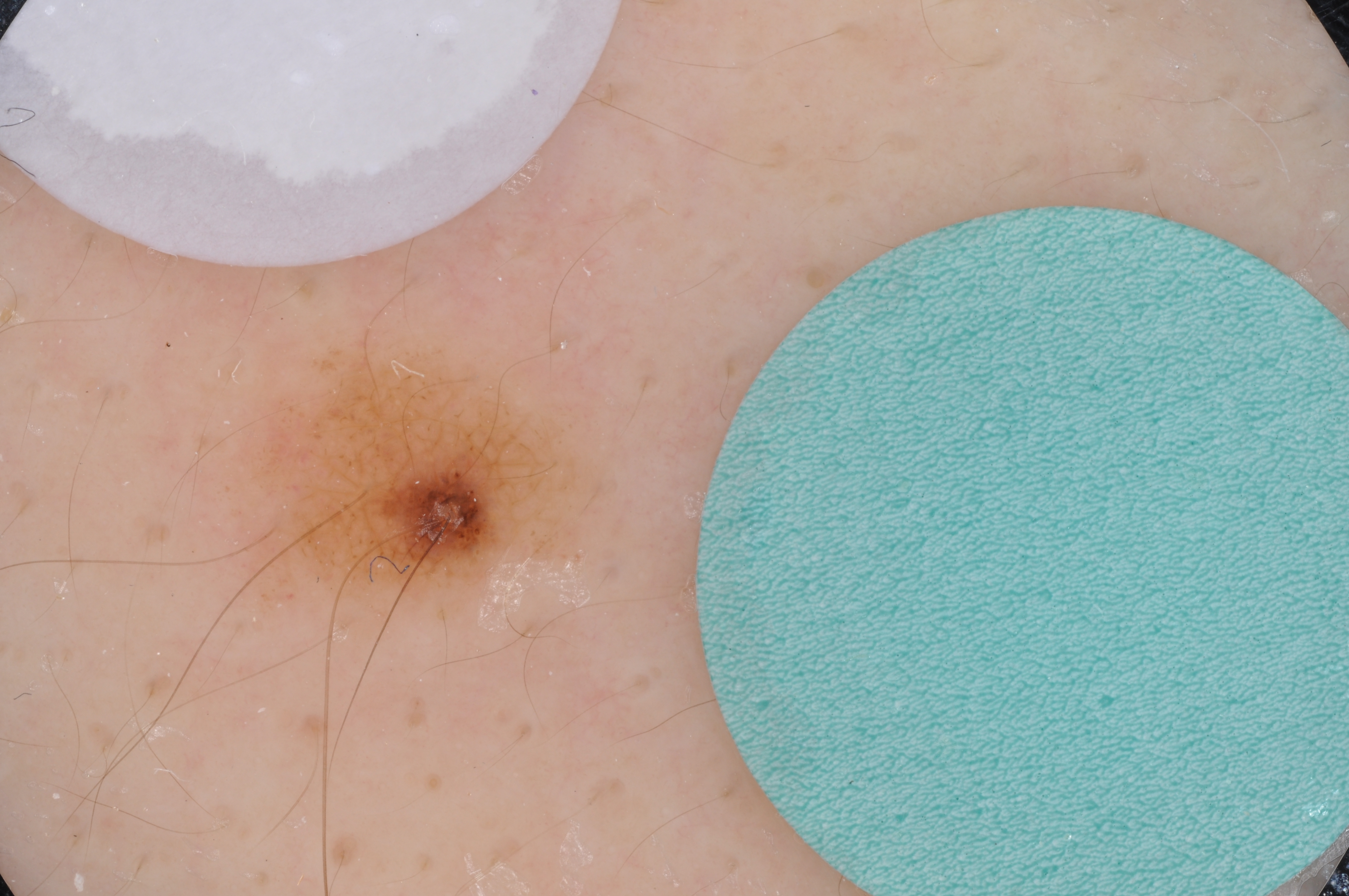image:
  modality: dermoscopy
lesion_location:
  bbox_xyxy:
    - 243
    - 331
    - 601
    - 663
lesion_extent: small
dermoscopic_features:
  present: []
  absent:
    - negative network
    - pigment network
    - milia-like cysts
    - globules
    - streaks
diagnosis:
  name: melanocytic nevus
  malignancy: benign
  lineage: melanocytic
  provenance: clinical